Dermoscopy of a skin lesion: 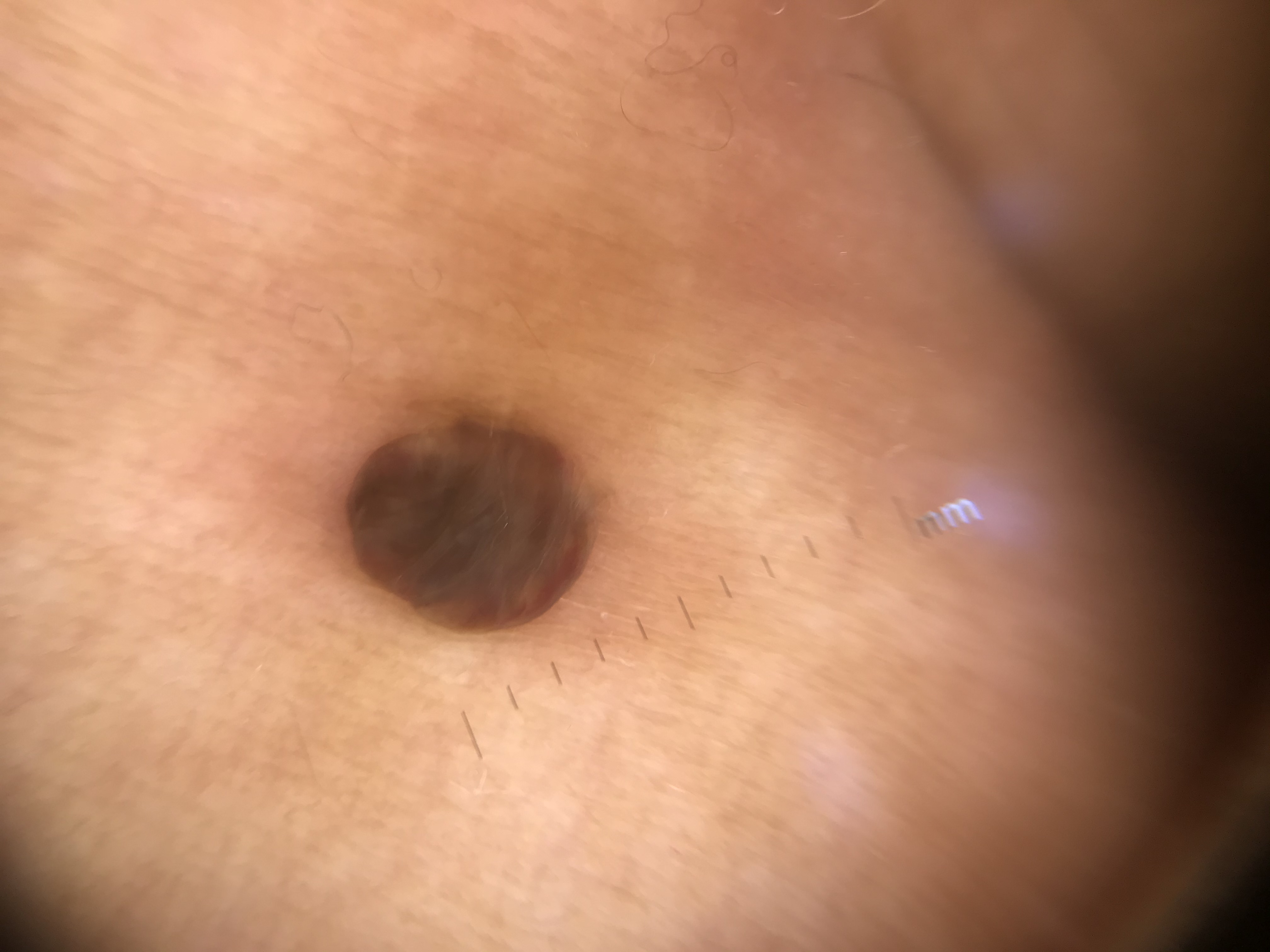Findings:
• diagnosis: dermal nevus (expert consensus)